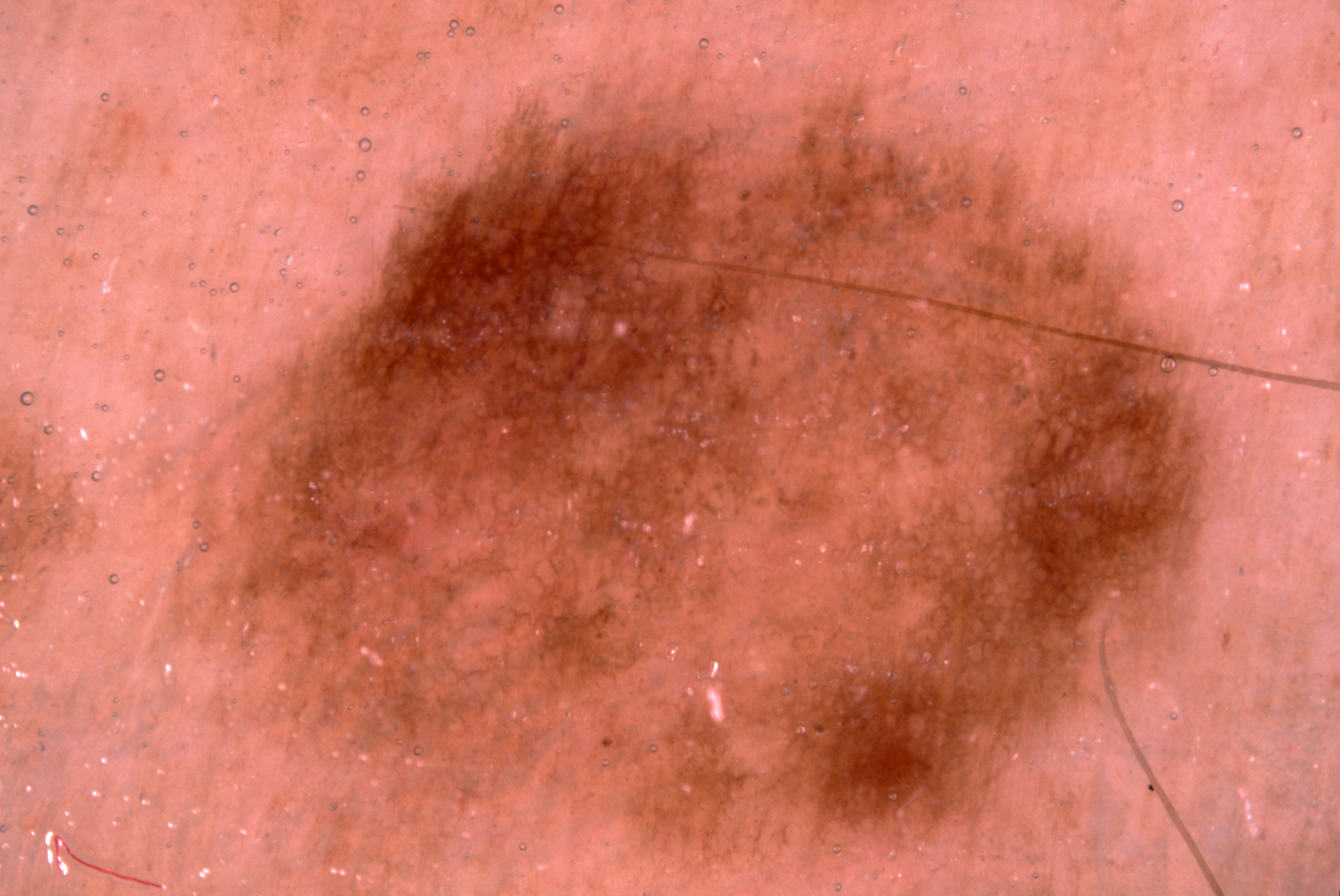Findings: A dermatoscopic image of a skin lesion. A female subject, approximately 65 years of age. Dermoscopic examination shows pigment network. As (left, top, right, bottom), the visible lesion spans bbox=[149, 45, 1238, 870]. Impression: The diagnostic assessment was a melanocytic nevus, a benign skin lesion.